A dermoscopy image of a single skin lesion:
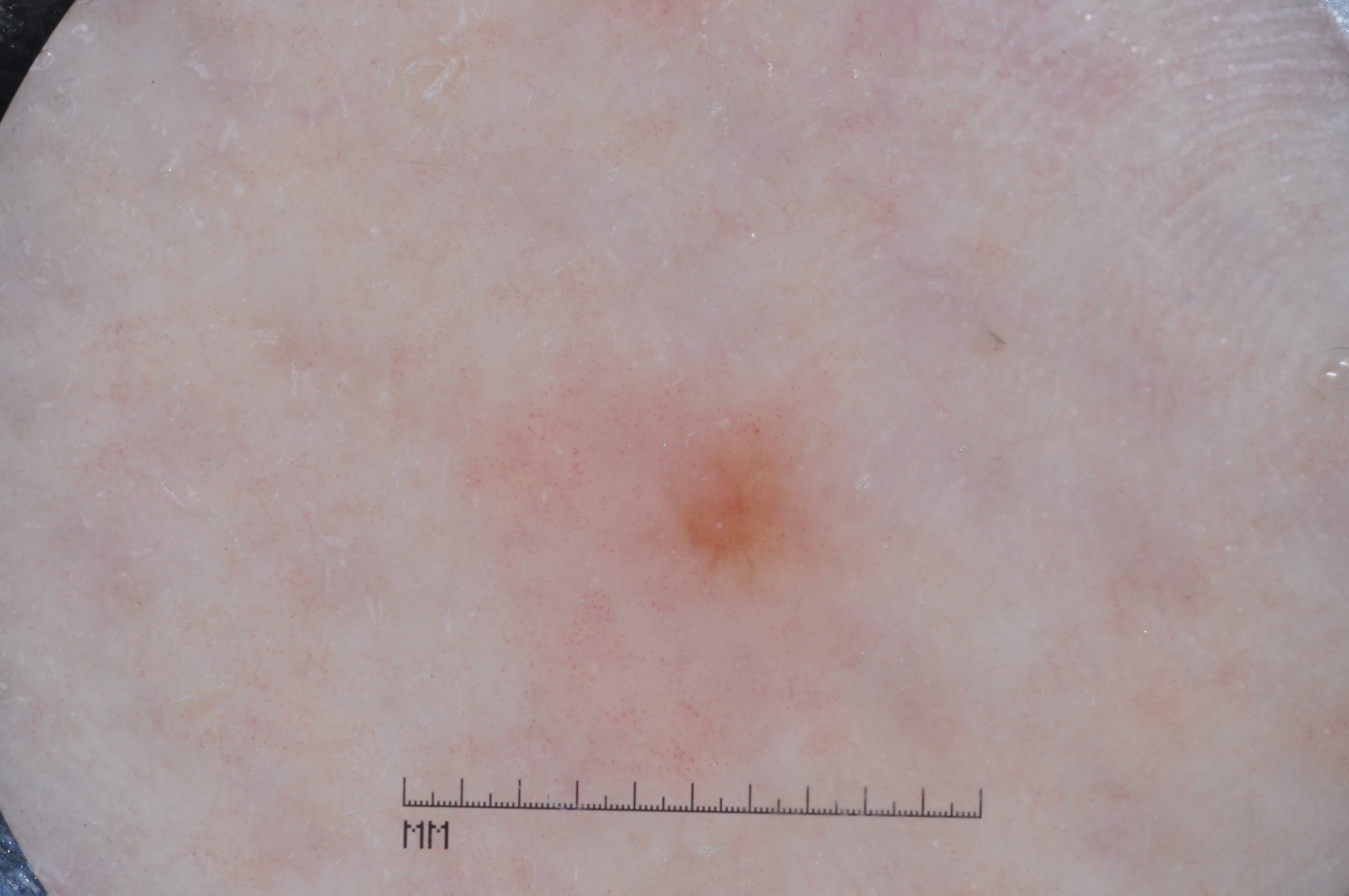{
  "lesion_location": {
    "bbox_xyxy": [
      437,
      313,
      953,
      813
    ]
  },
  "dermoscopic_features": {
    "present": [
      "pigment network",
      "milia-like cysts"
    ],
    "absent": [
      "streaks",
      "negative network"
    ]
  },
  "lesion_extent": {
    "approx_field_fraction_pct": 17
  },
  "diagnosis": {
    "name": "melanoma",
    "malignancy": "malignant",
    "lineage": "melanocytic",
    "provenance": "histopathology"
  }
}